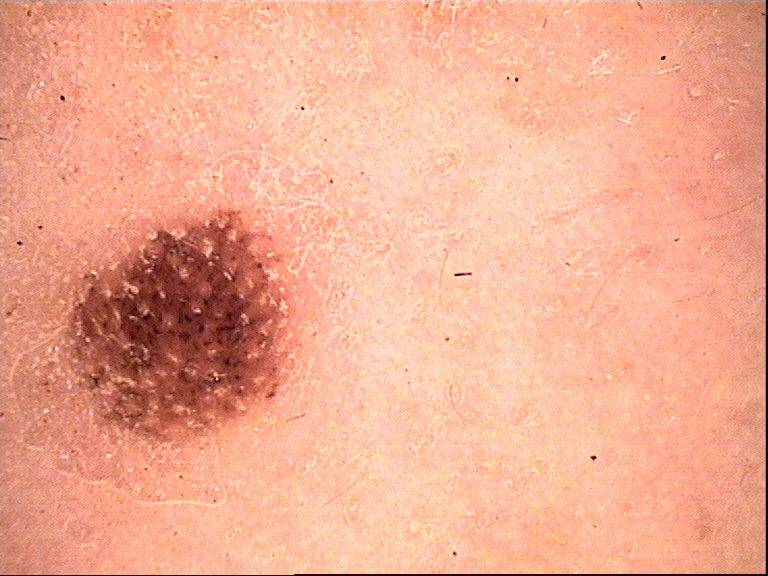Consistent with a benign lesion — a dysplastic junctional nevus.